The photograph was taken at a distance · the subject is a female aged 50–59 · located on the arm and back of the hand: 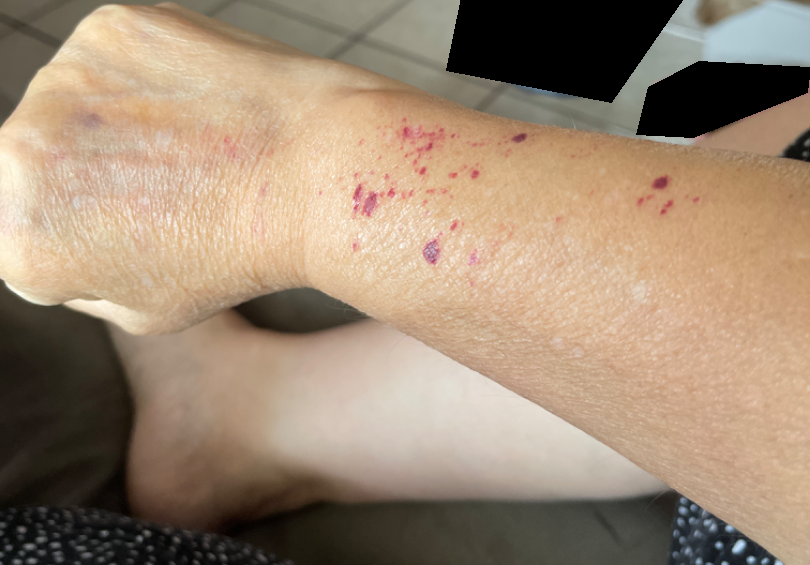| field | value |
|---|---|
| assessment | in keeping with ecchymoses |